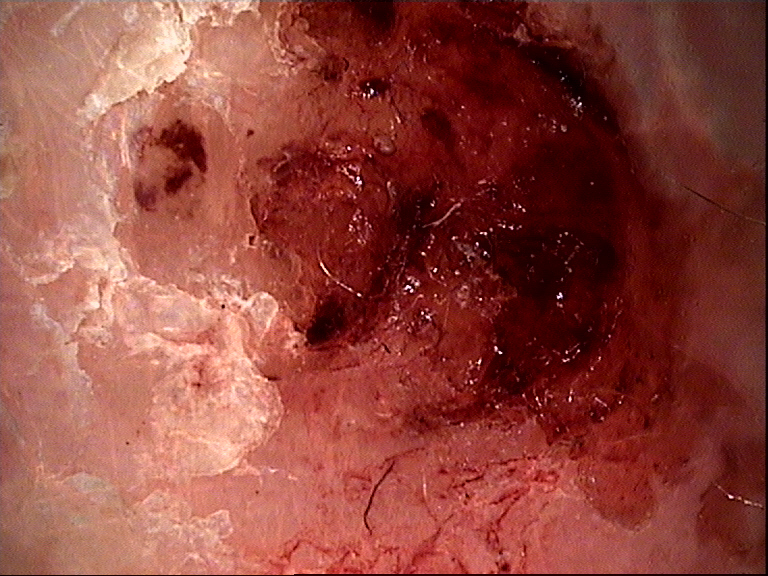Dermoscopy of a skin lesion. Confirmed on histopathology as a malignant, keratinocytic lesion — a squamous cell carcinoma.